A skin lesion imaged with a dermatoscope. A female subject, aged 38 to 42.
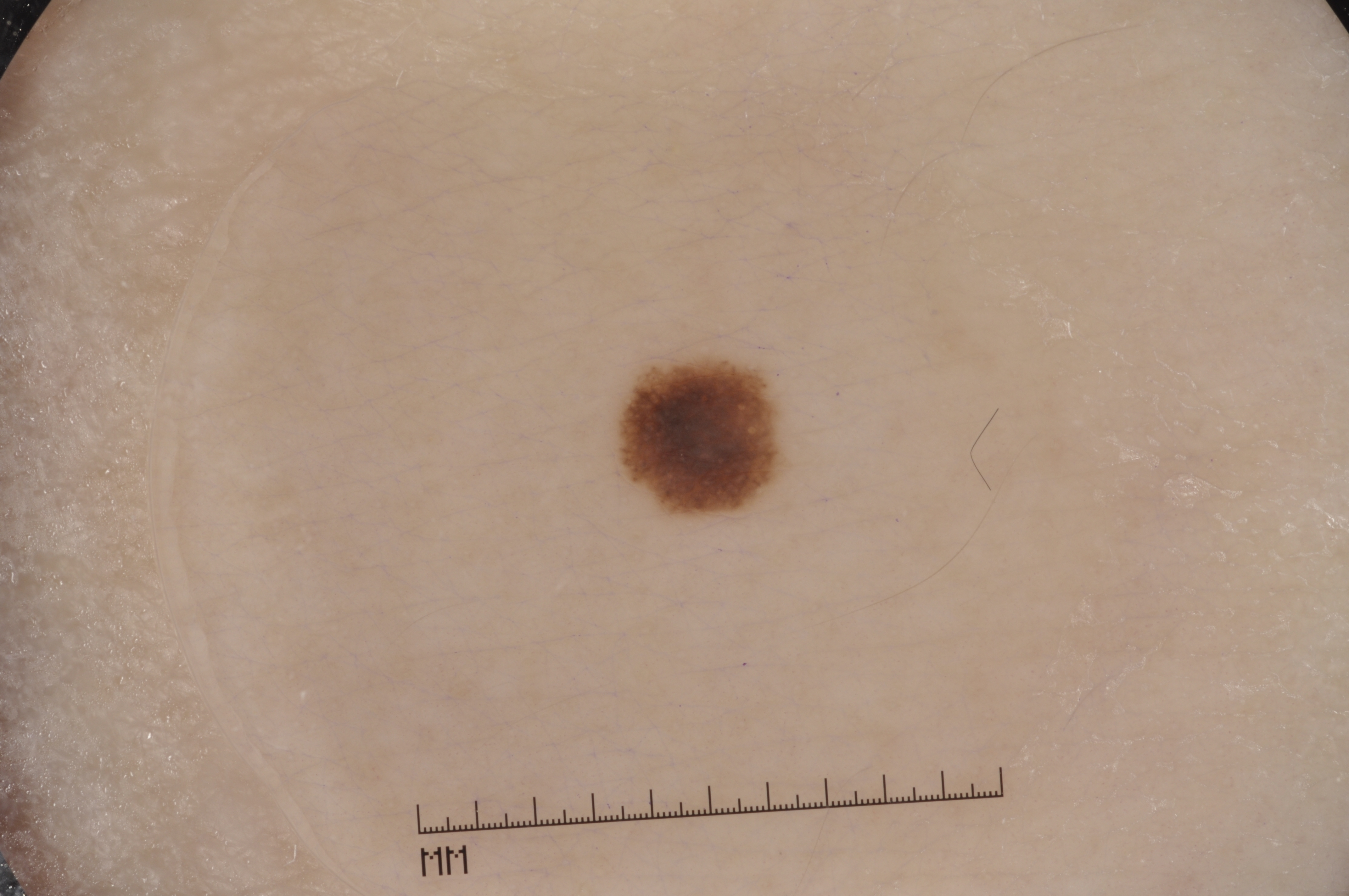With coordinates (x1, y1, x2, y2), the lesion's extent is 622 365 780 511.
Dermoscopic assessment notes pigment network, with no streaks, negative network, or milia-like cysts.
The lesion occupies roughly 2% of the field.
Clinically diagnosed as a melanocytic nevus.